Dermoscopy of a skin lesion: 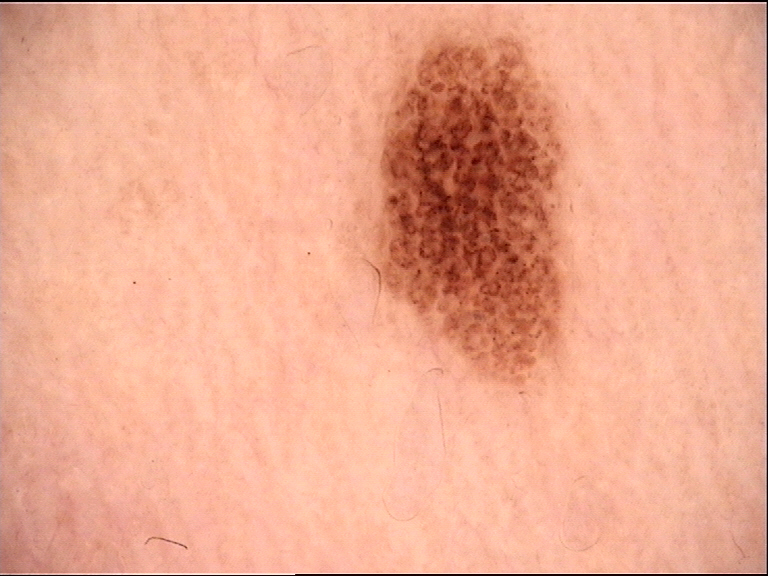Conclusion:
Labeled as a dysplastic junctional nevus.